A dermoscopy image of a single skin lesion.
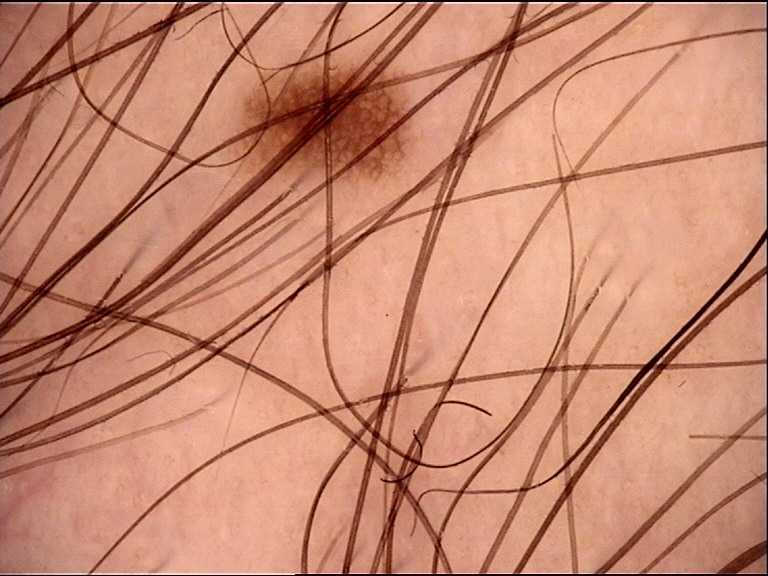• assessment · dysplastic junctional nevus (expert consensus)